The patient considered this a rash, texture is reported as raised or bumpy, present for one to four weeks, the lesion is associated with burning, this is a close-up image, located on the leg.
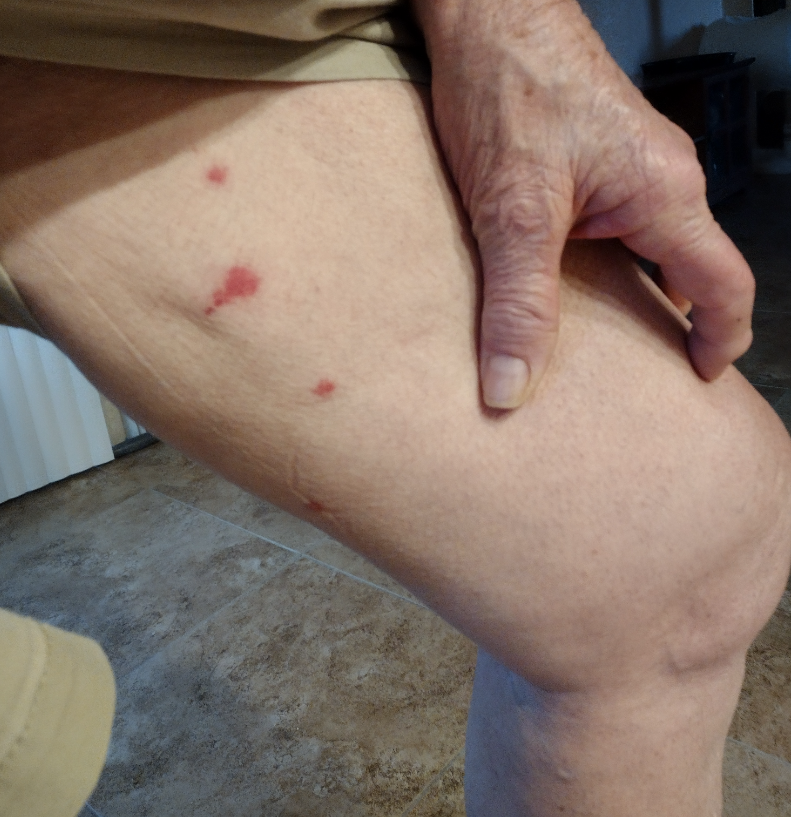  differential:
    Insect Bite: 0.67
    Hypersensitivity: 0.33